Dermoscopy of a skin lesion — 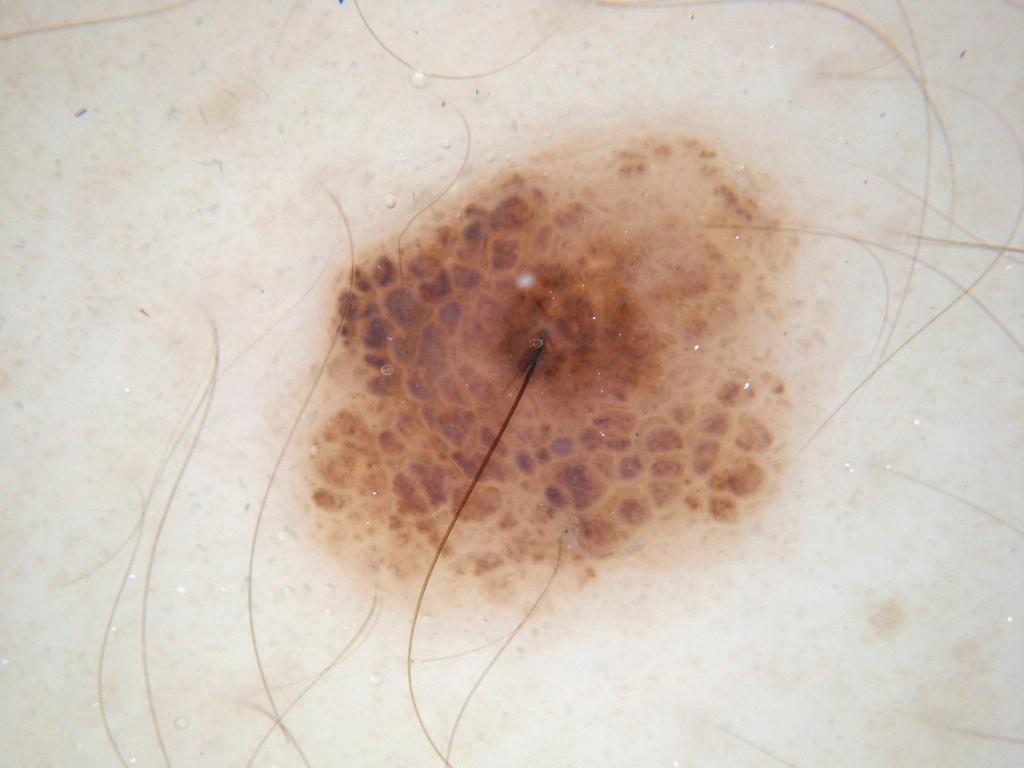A mid-sized lesion within the field. The visible lesion spans left=285, top=116, right=842, bottom=627. The clinical diagnosis was a benign skin lesion.